By self-report, a personal history of cancer, no sunbed use, and no family history of skin cancer. The patient says their skin reddens with sun exposure. The patient describes having numerous moles. A male subject age 73. Collected as part of a research study, without a referral diagnosis.
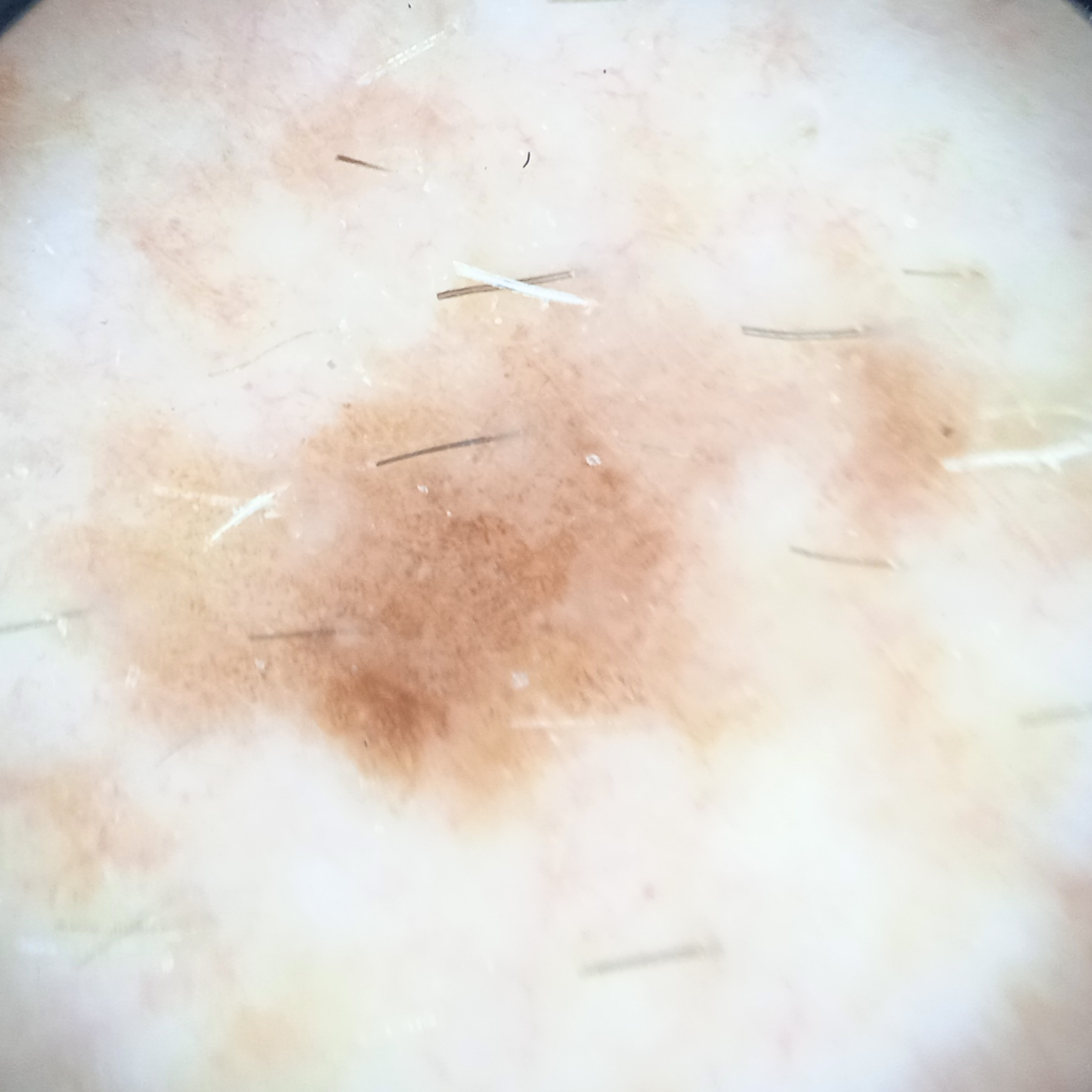Findings: The lesion involves the torso. Conclusion: Dermatologist review favored a melanoma.